A skin lesion imaged with a dermatoscope.
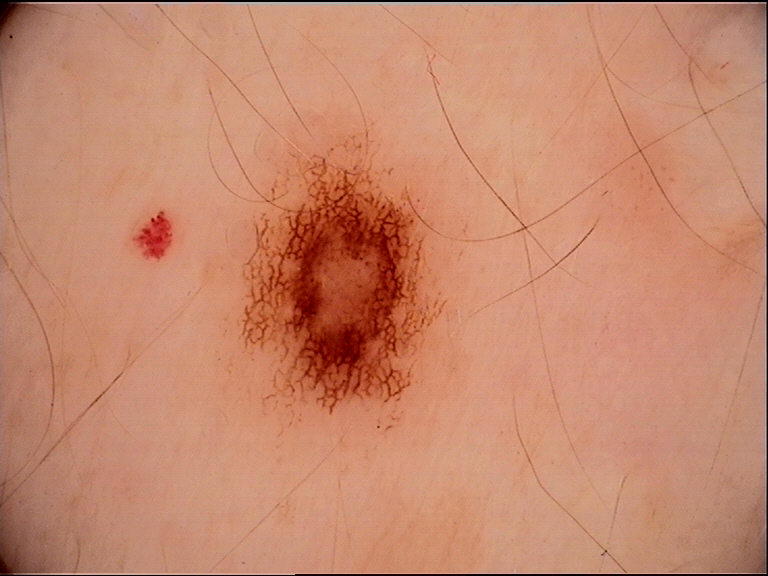Impression: Consistent with a dysplastic junctional nevus.